A dermoscopic close-up of a skin lesion: 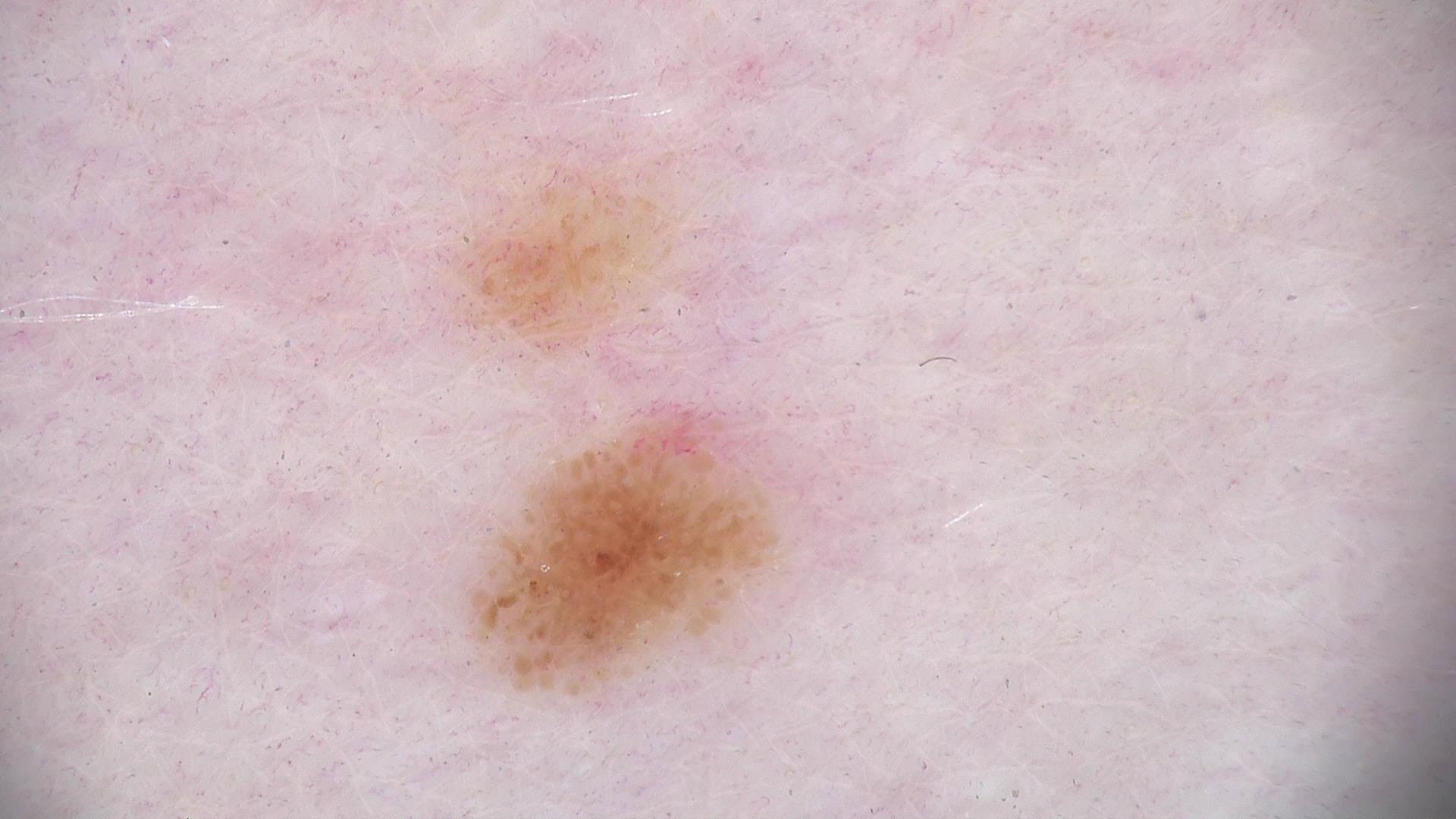diagnostic label — dysplastic junctional nevus (expert consensus)